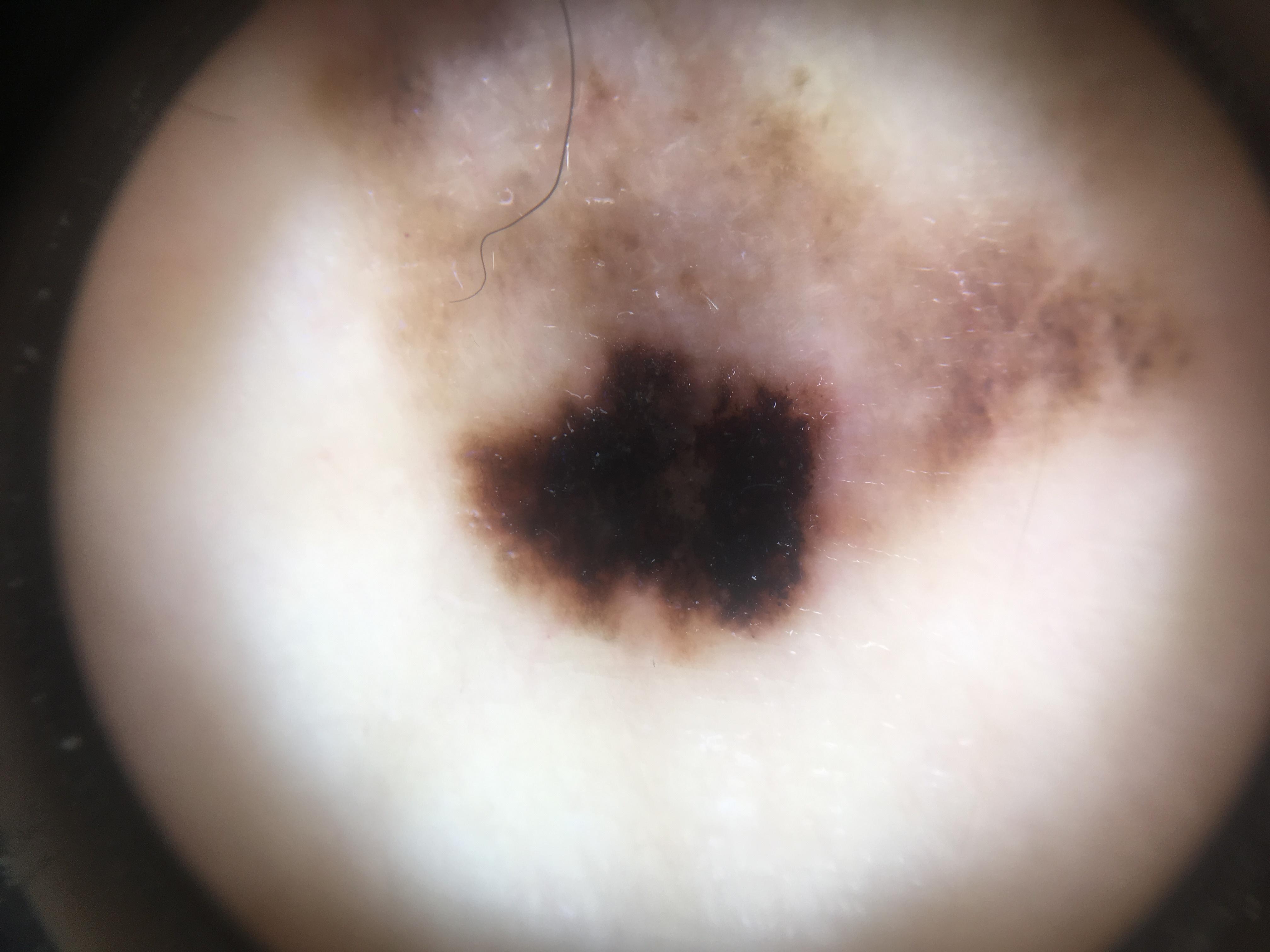Summary:
The patient is Fitzpatrick skin type II. A skin lesion imaged with a dermatoscope. A male subject aged around 80. Located on the trunk.
Diagnosis:
Histopathological examination showed a melanoma.